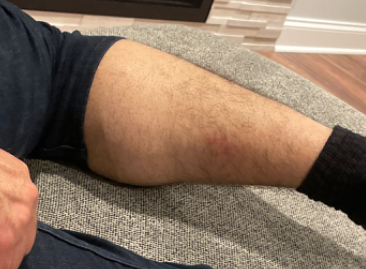Review: The image was not sufficient for the reviewer to characterize the skin condition.